A female subject 64 years of age; the patient says their skin tans without first burning; on a questionnaire the patient reported a family history of skin cancer and a personal history of cancer; referred for assessment of suspected seborrheic keratosis; the patient describes having a moderate number of moles; dermoscopy of a skin lesion — 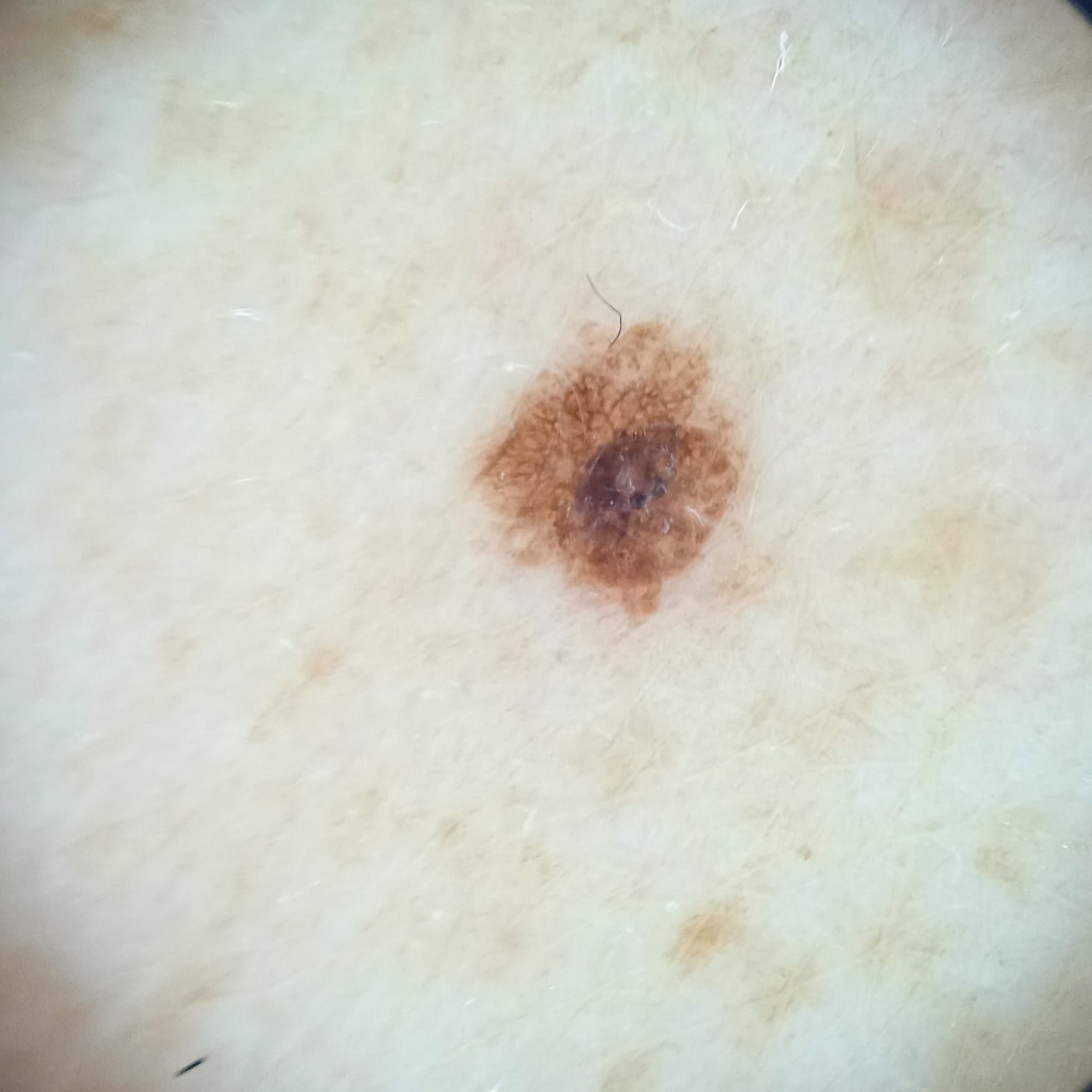Findings:
The lesion involves the back. The lesion is about 3.5 mm across.
Diagnosis:
Histopathologically confirmed as a seborrheic keratosis, following excision.